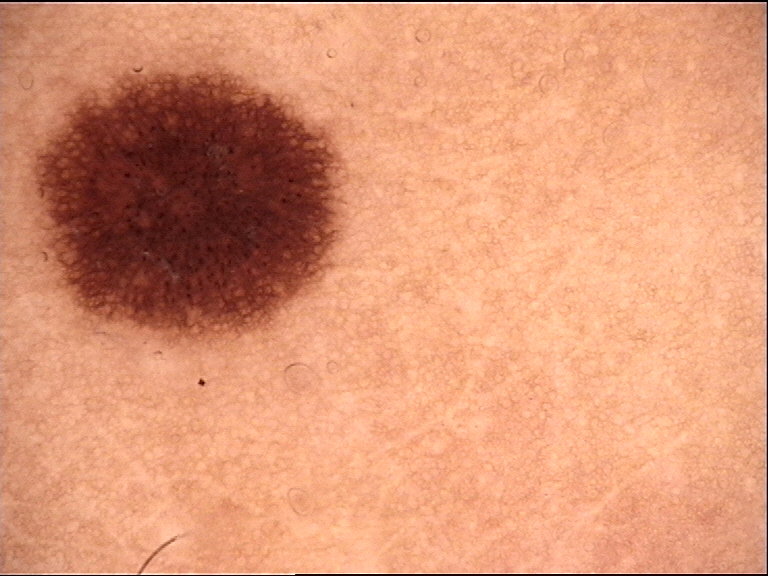Q: What is the imaging modality?
A: dermatoscopy
Q: How is the lesion classified?
A: banal
Q: What was the diagnostic impression?
A: junctional nevus (expert consensus)